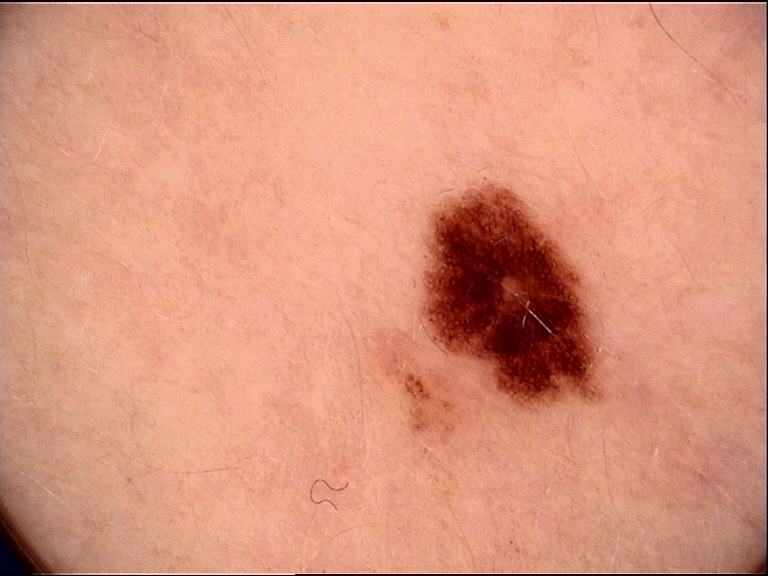Classified as a dysplastic junctional nevus.